The back of the torso is involved; the photo was captured at an angle; the patient is 40–49, female.
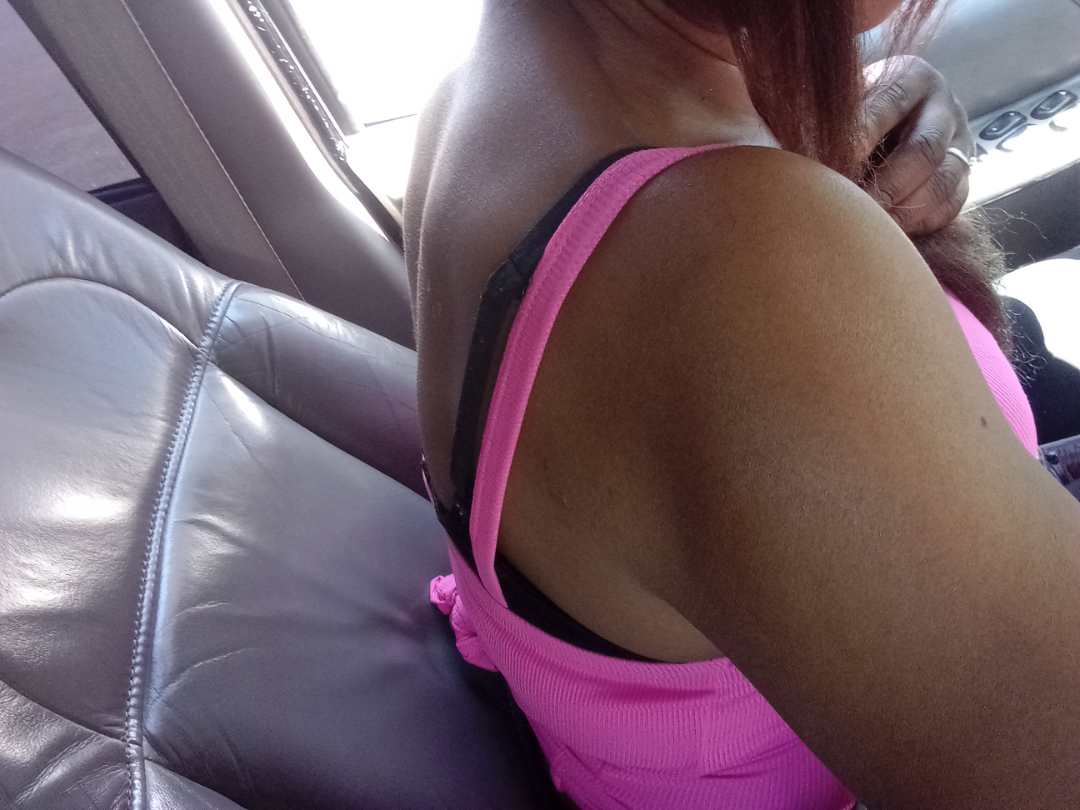Case summary:
* assessment — ungradable on photographic review